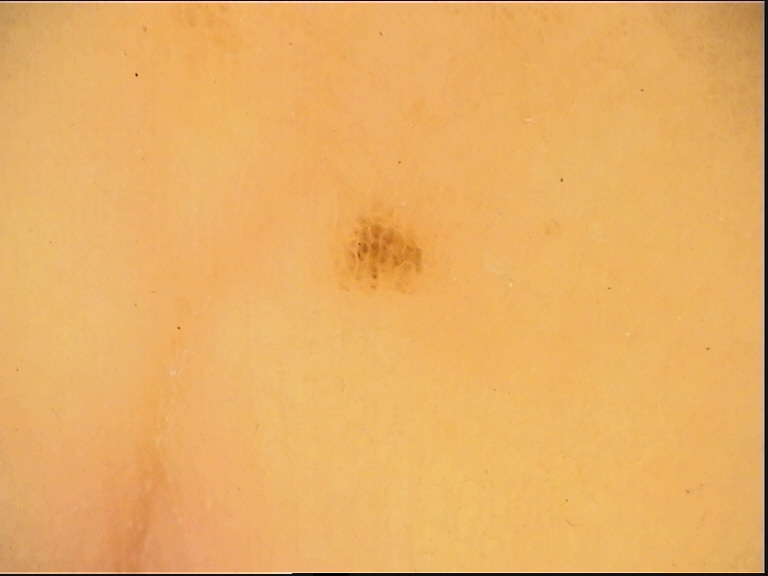image type = dermoscopy; classification = banal; assessment = acral junctional nevus (expert consensus).